A female patient approximately 45 years of age; a dermoscopy image of a single skin lesion: 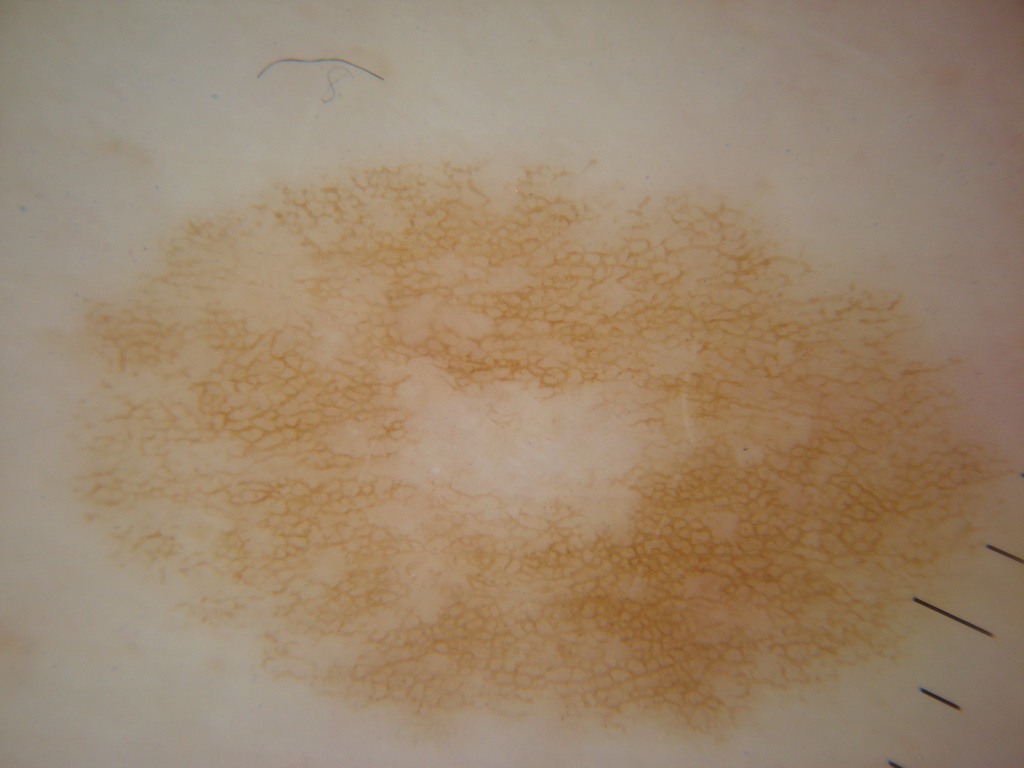<lesion>
<dermoscopic_features>
  <present>pigment network</present>
  <absent>streaks, globules, milia-like cysts, negative network</absent>
</dermoscopic_features>
<lesion_location>
  <bbox_xyxy>64, 155, 1016, 747</bbox_xyxy>
</lesion_location>
<diagnosis>
  <name>melanocytic nevus</name>
  <malignancy>benign</malignancy>
  <lineage>melanocytic</lineage>
  <provenance>clinical</provenance>
</diagnosis>
</lesion>